Dermoscopy of a skin lesion.
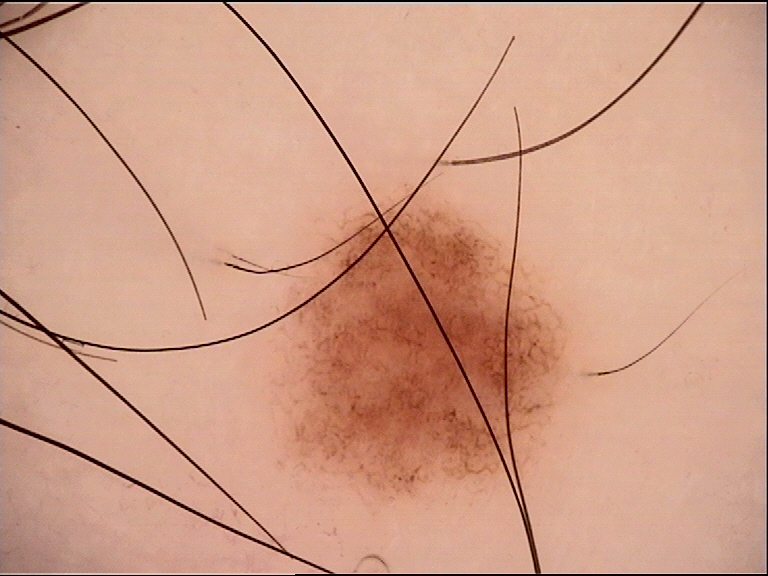<dermoscopy>
<diagnosis>
<name>dysplastic junctional nevus</name>
<code>jd</code>
<malignancy>benign</malignancy>
<super_class>melanocytic</super_class>
<confirmation>expert consensus</confirmation>
</diagnosis>
</dermoscopy>